A dermoscopic image of a skin lesion:
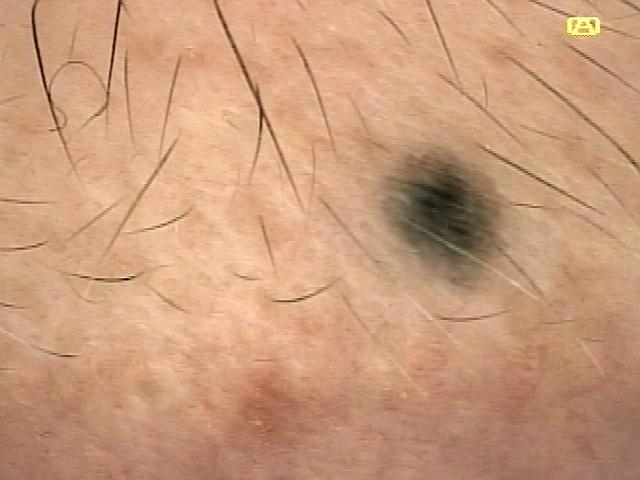| key | value |
|---|---|
| anatomic site | the head or neck |
| assessment | Nevus |